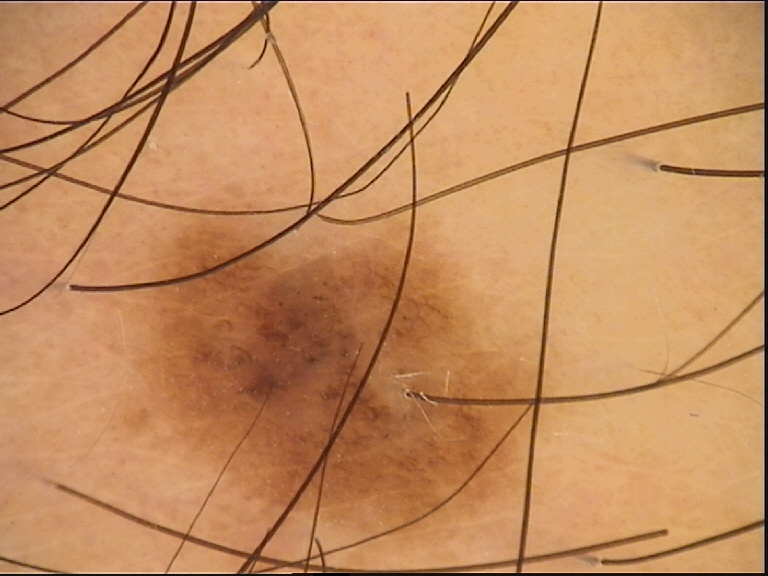A dermoscopic close-up of a skin lesion.
Consistent with a dysplastic compound nevus.